A dermoscopic close-up of a skin lesion.
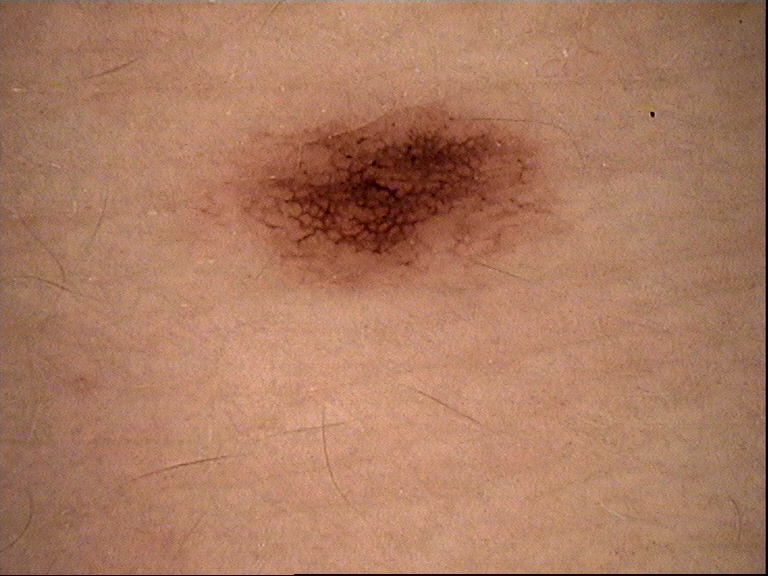• label — dysplastic junctional nevus (expert consensus)